The patient says their skin reddens painfully with sun exposure; a moderate number of moles by the patient's own estimate; a female patient aged 35; acquired for a research image collection, with no referral diagnosis — 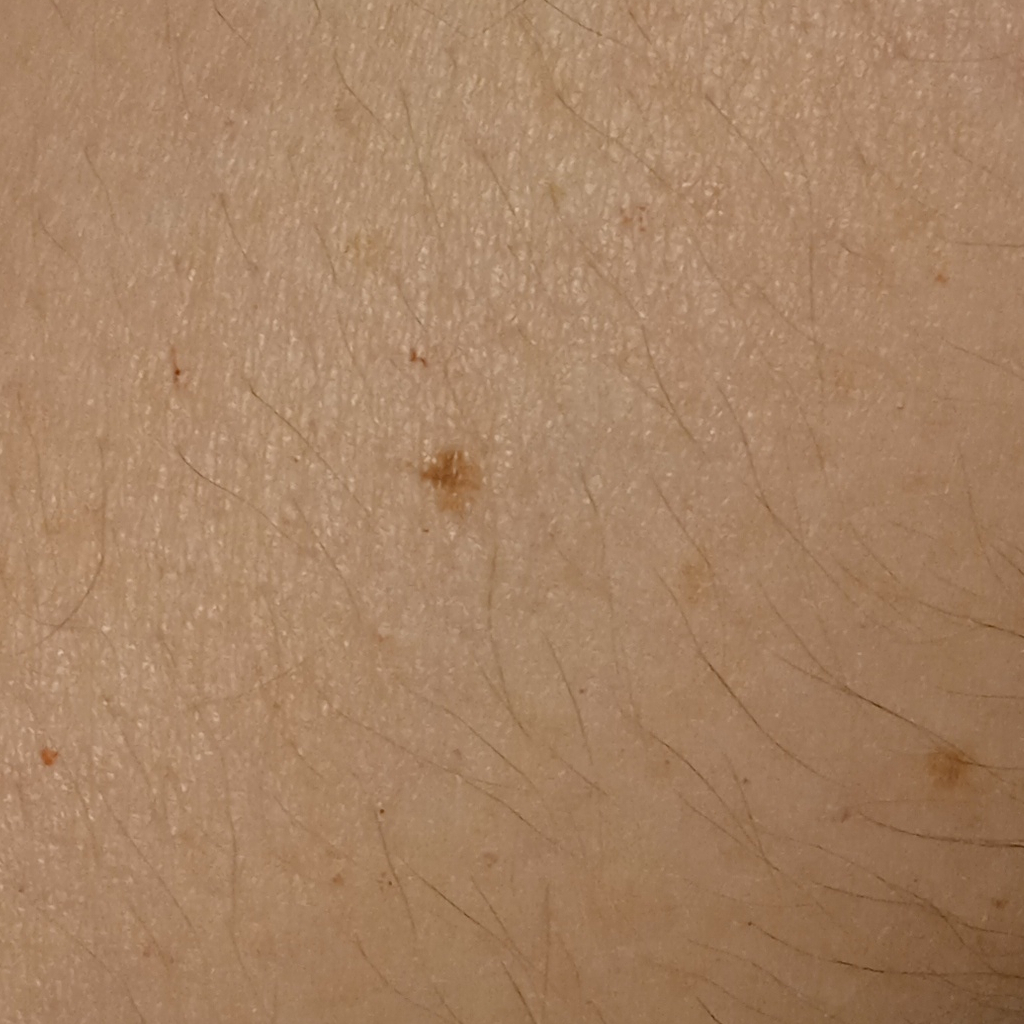Located on an arm. Dermatologist review favored a melanocytic nevus.